A dermoscopy image of a single skin lesion.
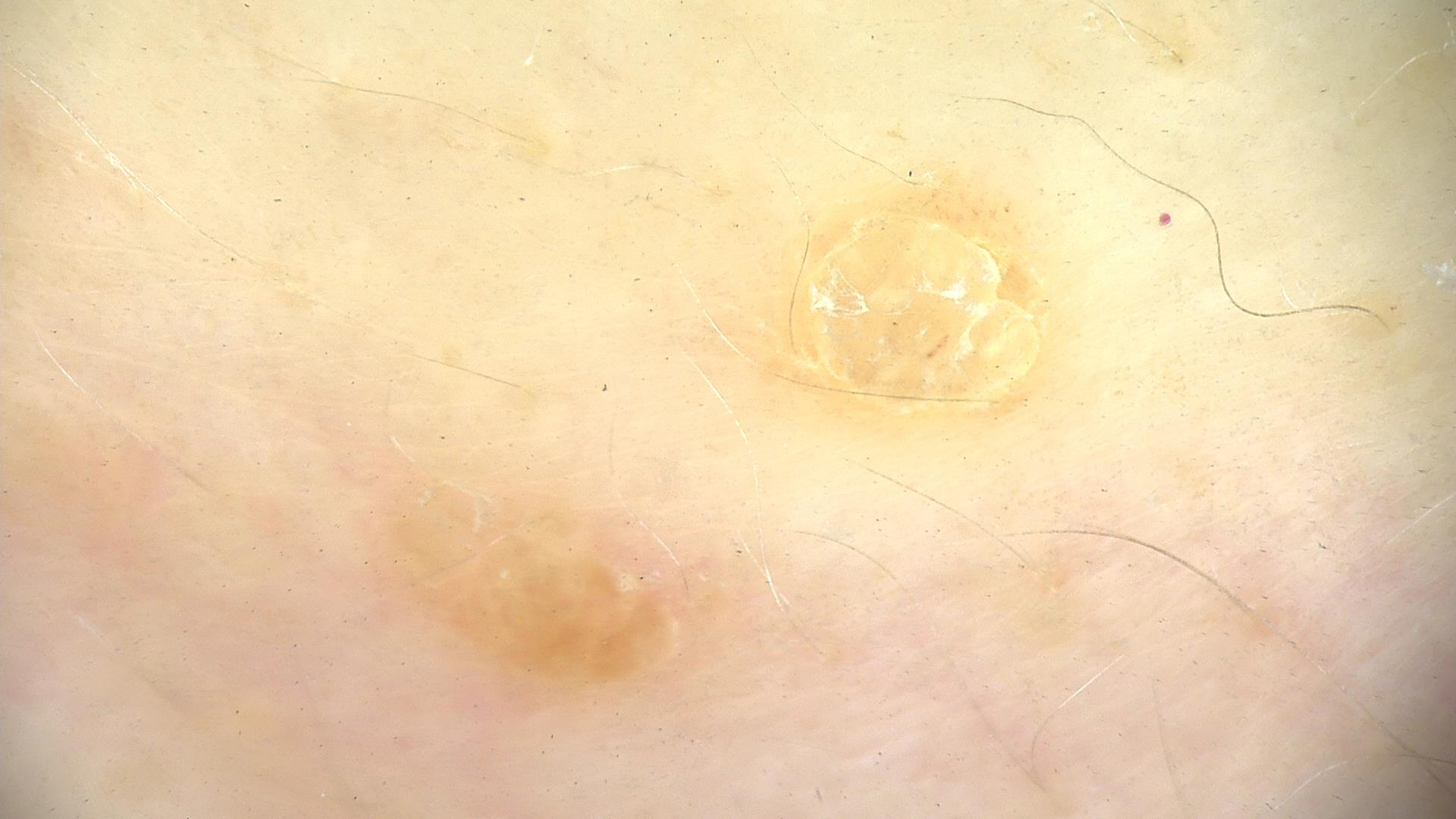| feature | finding |
|---|---|
| class | seborrheic keratosis (expert consensus) |